A dermoscopy image of a skin lesion; the patient describes having few moles overall; acquired for a research image collection, with no referral diagnosis; on a questionnaire the patient reported a personal history of cancer; a male patient 72 years old; the patient says their skin reddens with sun exposure: 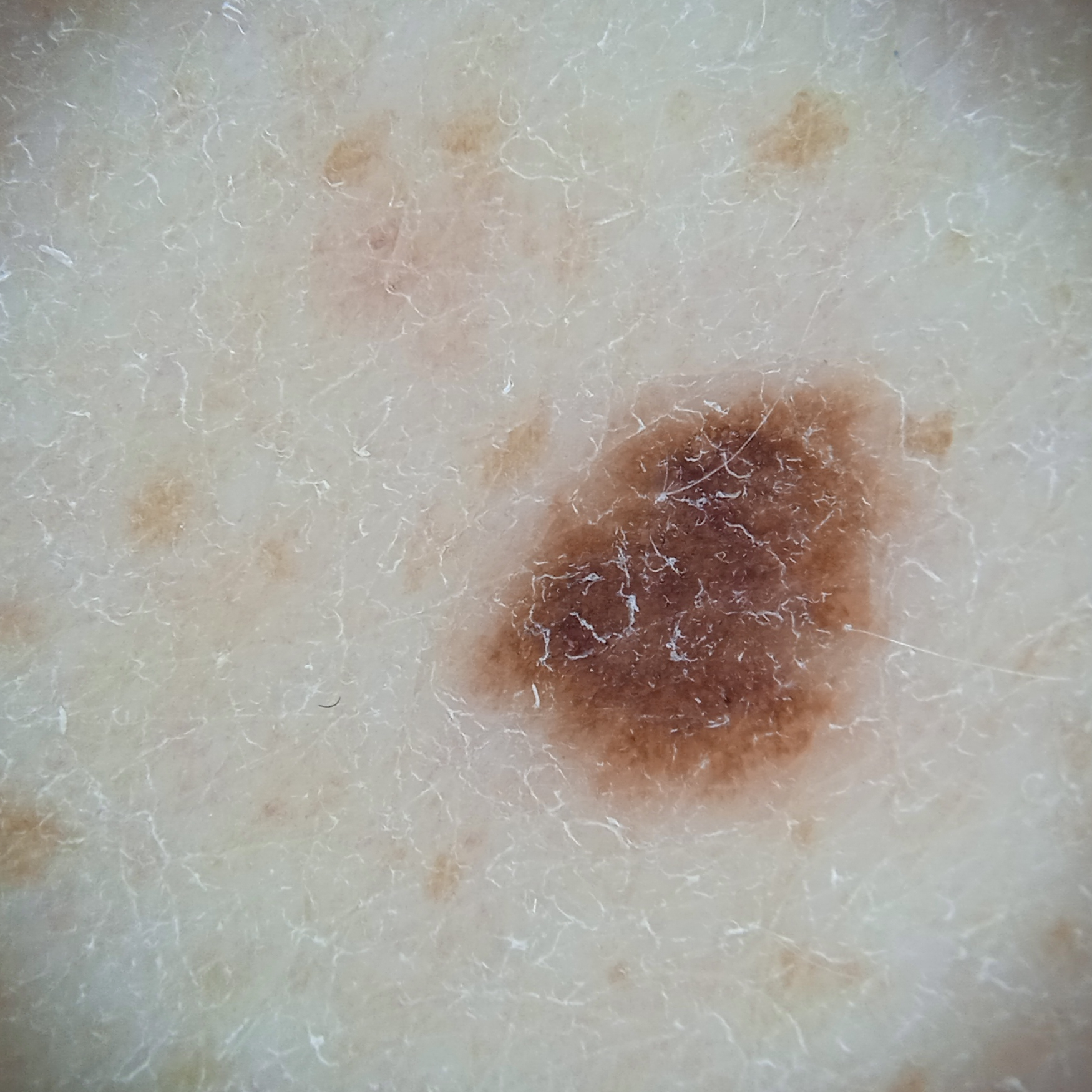size: 5.6 mm, diagnostic label: melanocytic nevus (dermatologist consensus).